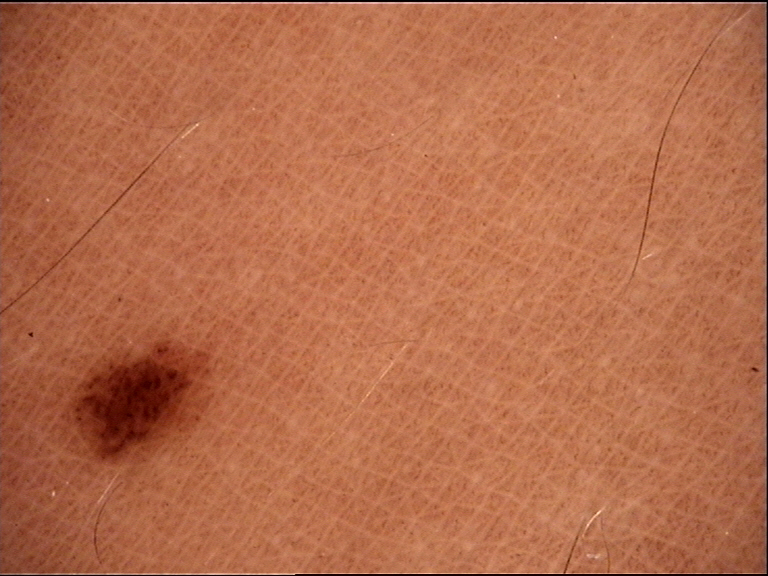Findings:
A dermoscopic image of a skin lesion. The architecture is that of a banal lesion.
Conclusion:
Labeled as a junctional nevus.